The contributor is a female aged 50–59 · located on the back of the torso and front of the torso · the photograph was taken at a distance — 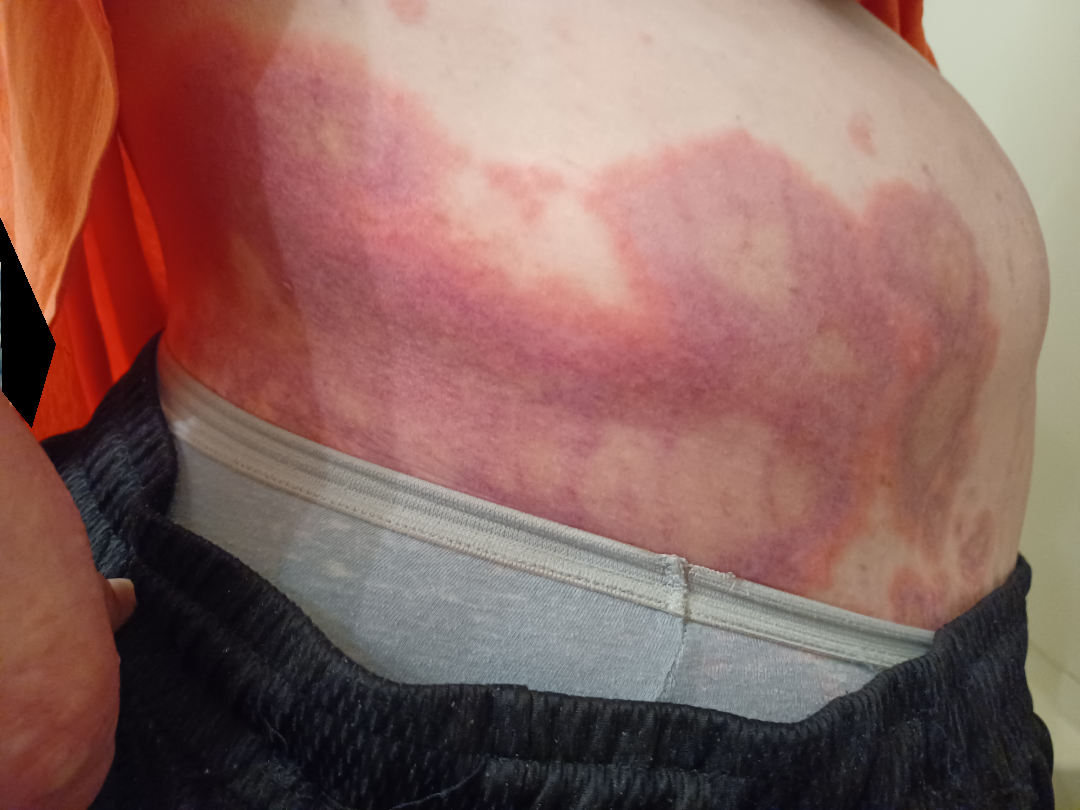Diagnostic features were not clearly distinguishable in this photograph.